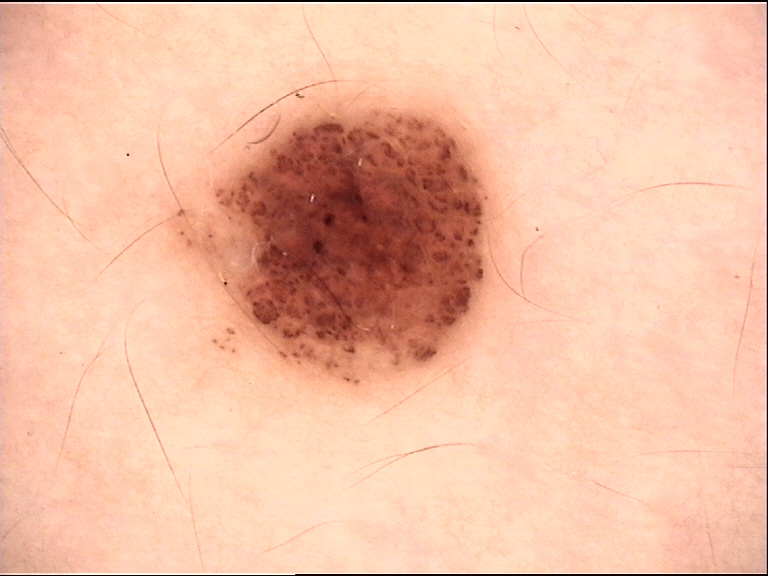Q: What kind of image is this?
A: dermoscopy
Q: What is this lesion?
A: compound nevus (expert consensus)